A clinical photo of a skin lesion taken with a smartphone:
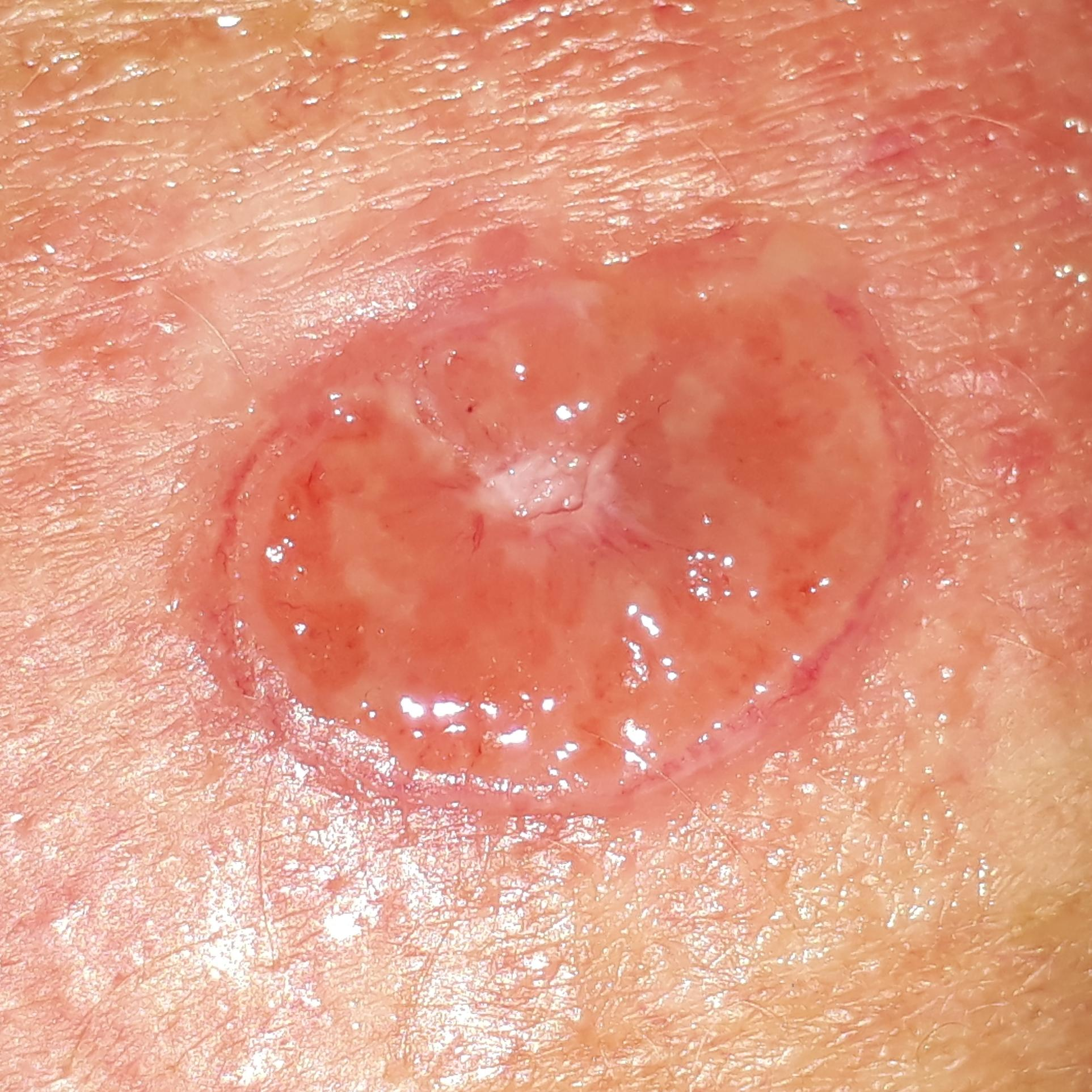Q: Where on the body is the lesion?
A: the back
Q: What is this lesion?
A: basal cell carcinoma (biopsy-proven)